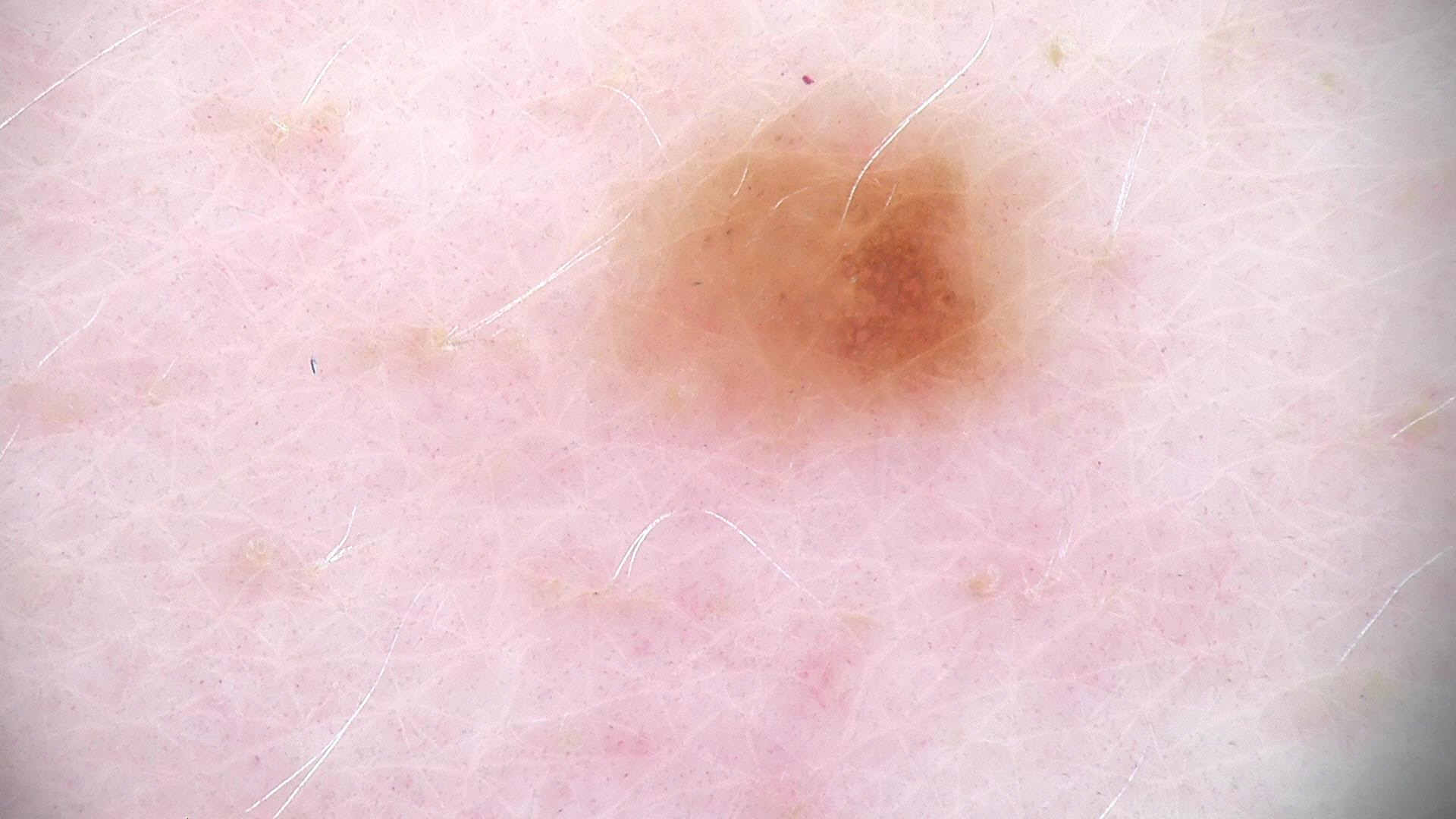A dermoscopic photograph of a skin lesion. The diagnostic label was a dysplastic junctional nevus.